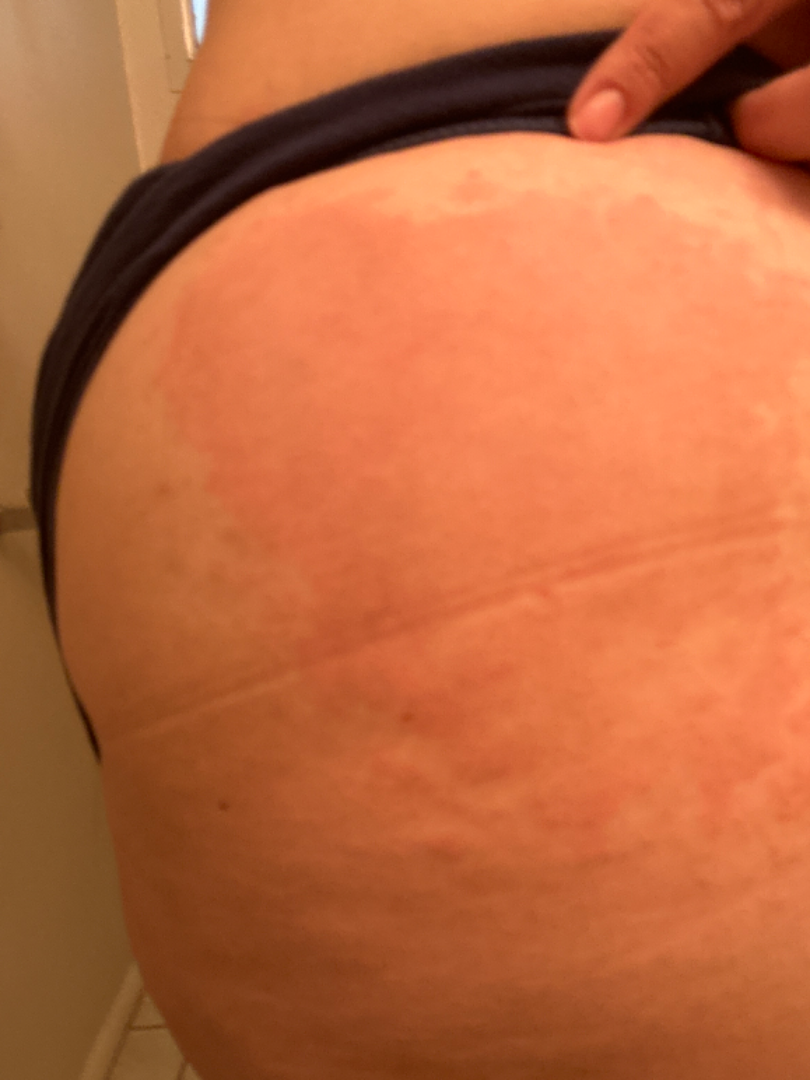patient-reported symptoms = itching, darkening and enlargement | subject = female, age 30–39 | surface texture = flat | view = at a distance | present for = one to four weeks | site = leg | impression = most likely Allergic Contact Dermatitis; also consider Cellulitis; an alternative is Erythema migrans.